Collected as part of a research study, without a referral diagnosis. A male patient age 83: 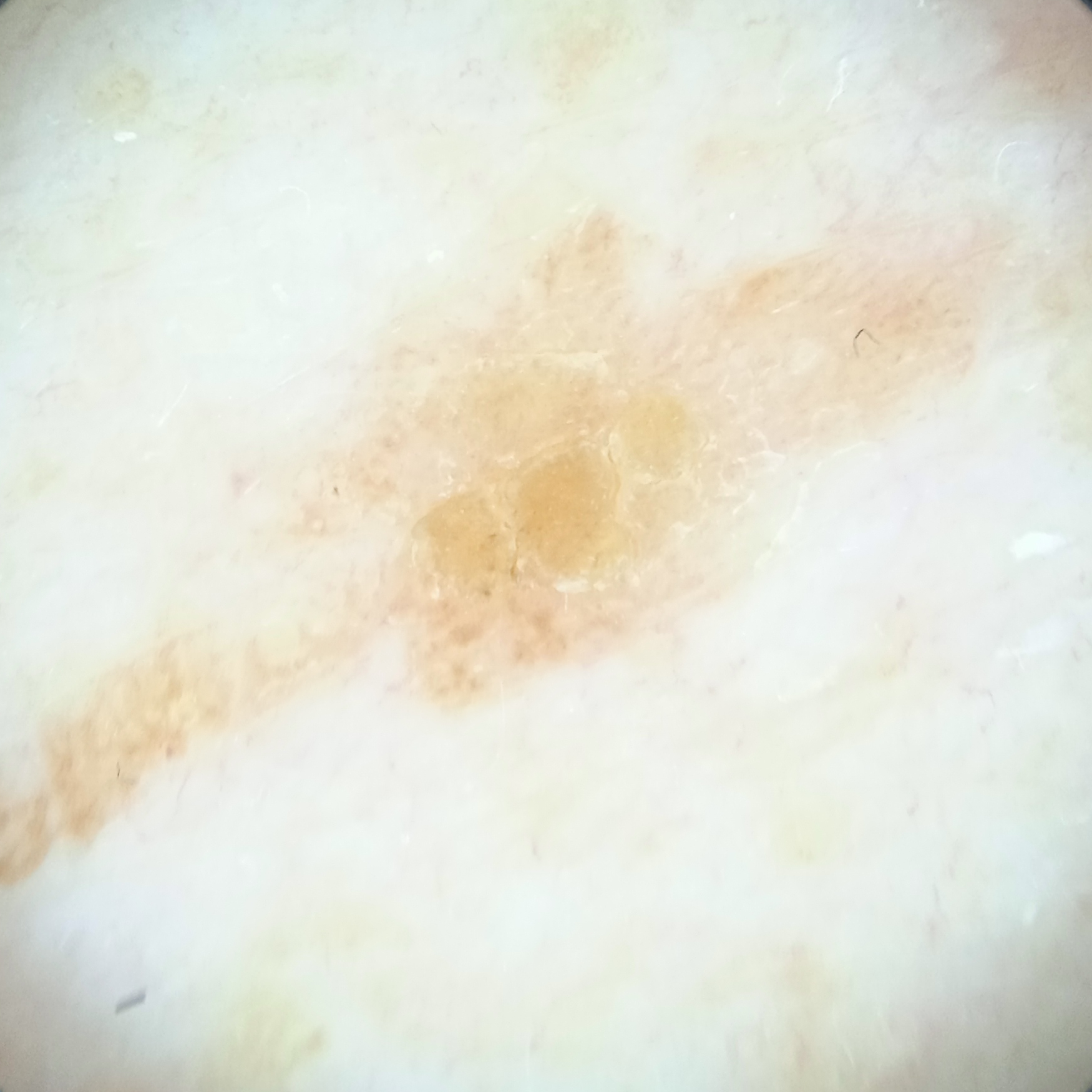Q: Where is the lesion?
A: the back
Q: What was the diagnosis?
A: seborrheic keratosis (dermatologist consensus)